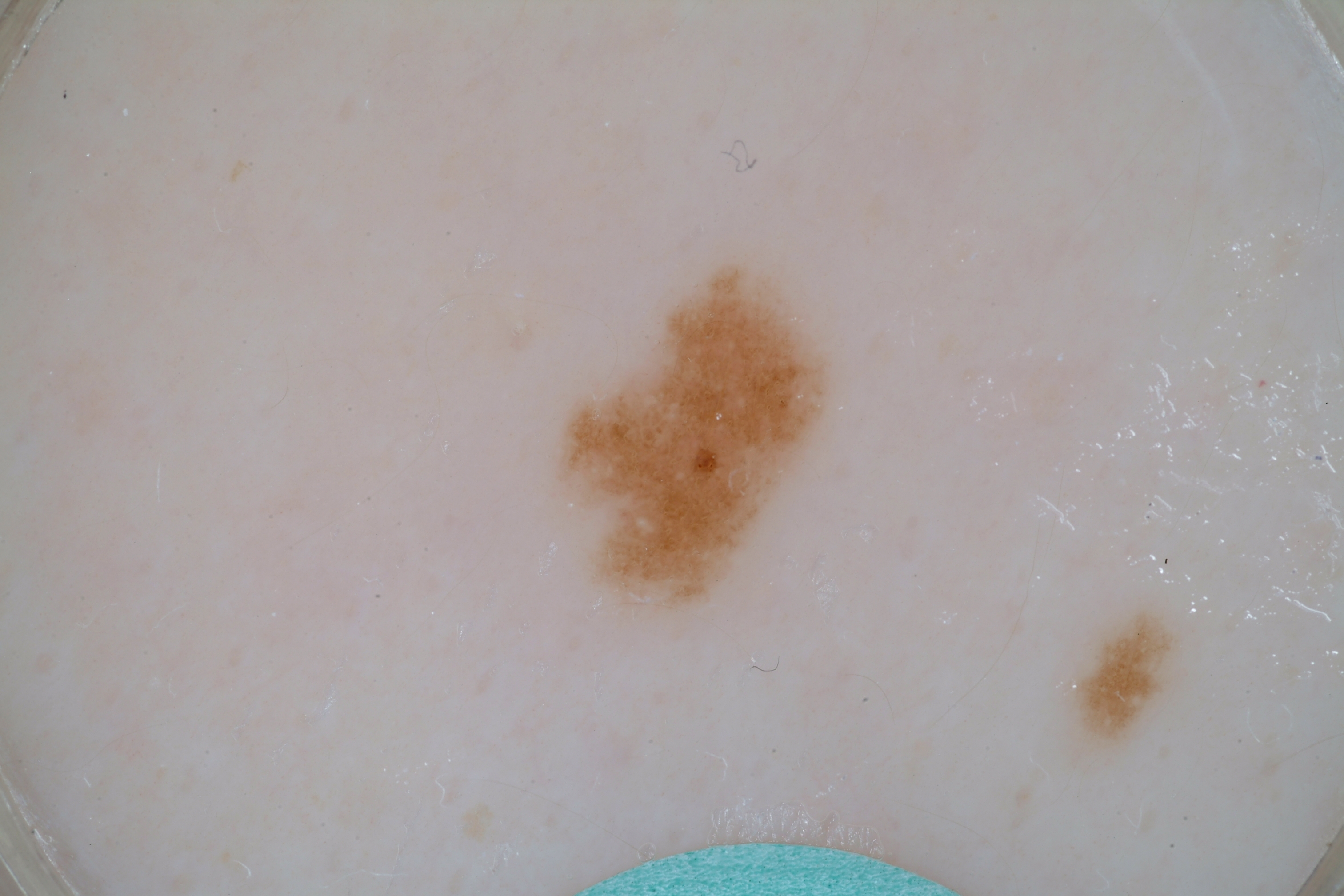A dermoscopy image of a single skin lesion. A female patient, aged 13 to 17. The lesion occupies roughly 5% of the field. Dermoscopic assessment notes negative network, globules, and milia-like cysts. The lesion is bounded by x1=550 y1=254 x2=837 y2=621. The lesion was assessed as a melanocytic nevus.